A male patient in their 50s, a dermoscopic image of a skin lesion:
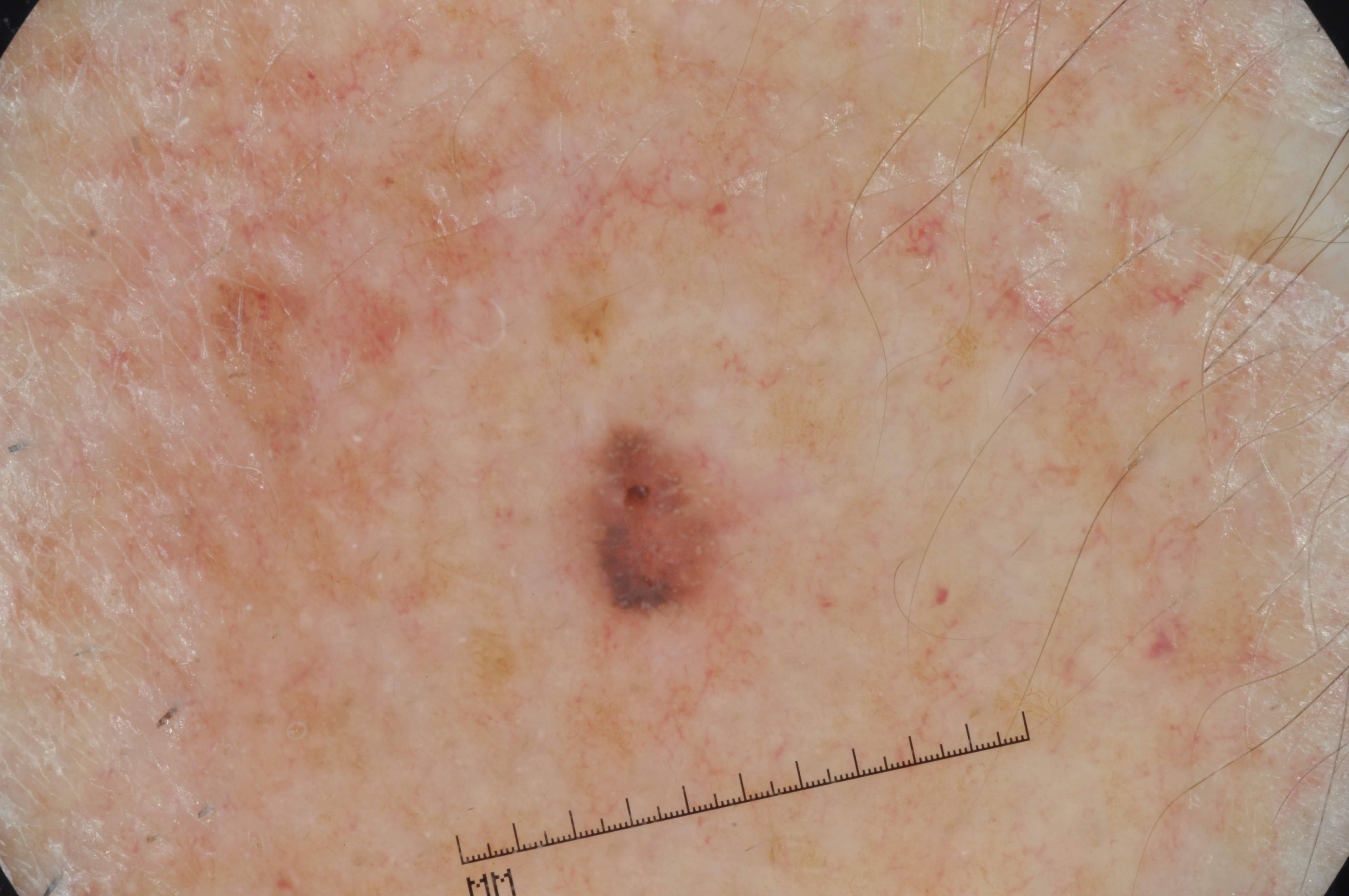On dermoscopy, the lesion shows no streaks, negative network, pigment network, or milia-like cysts.
The lesion occupies roughly 3% of the field.
In (x1, y1, x2, y2) order, the lesion is located at (550, 417, 762, 670).
Biopsy-confirmed as a melanoma.